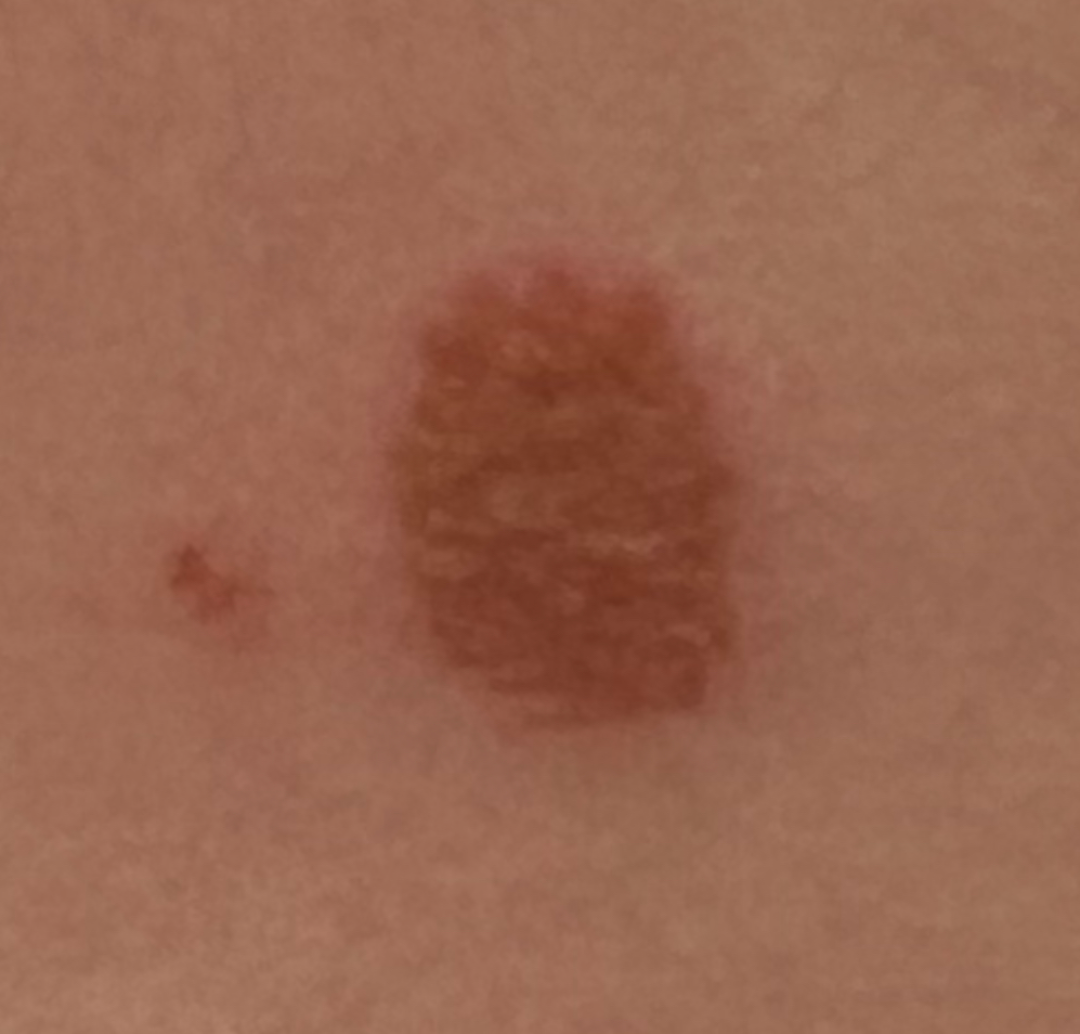  assessment: unable to determine
  texture: raised or bumpy
  shot_type: close-up
  skin_tone:
    monk_skin_tone:
      - 3
      - 4
  duration: about one day
  body_site: back of the torso